A skin lesion imaged with a dermatoscope.
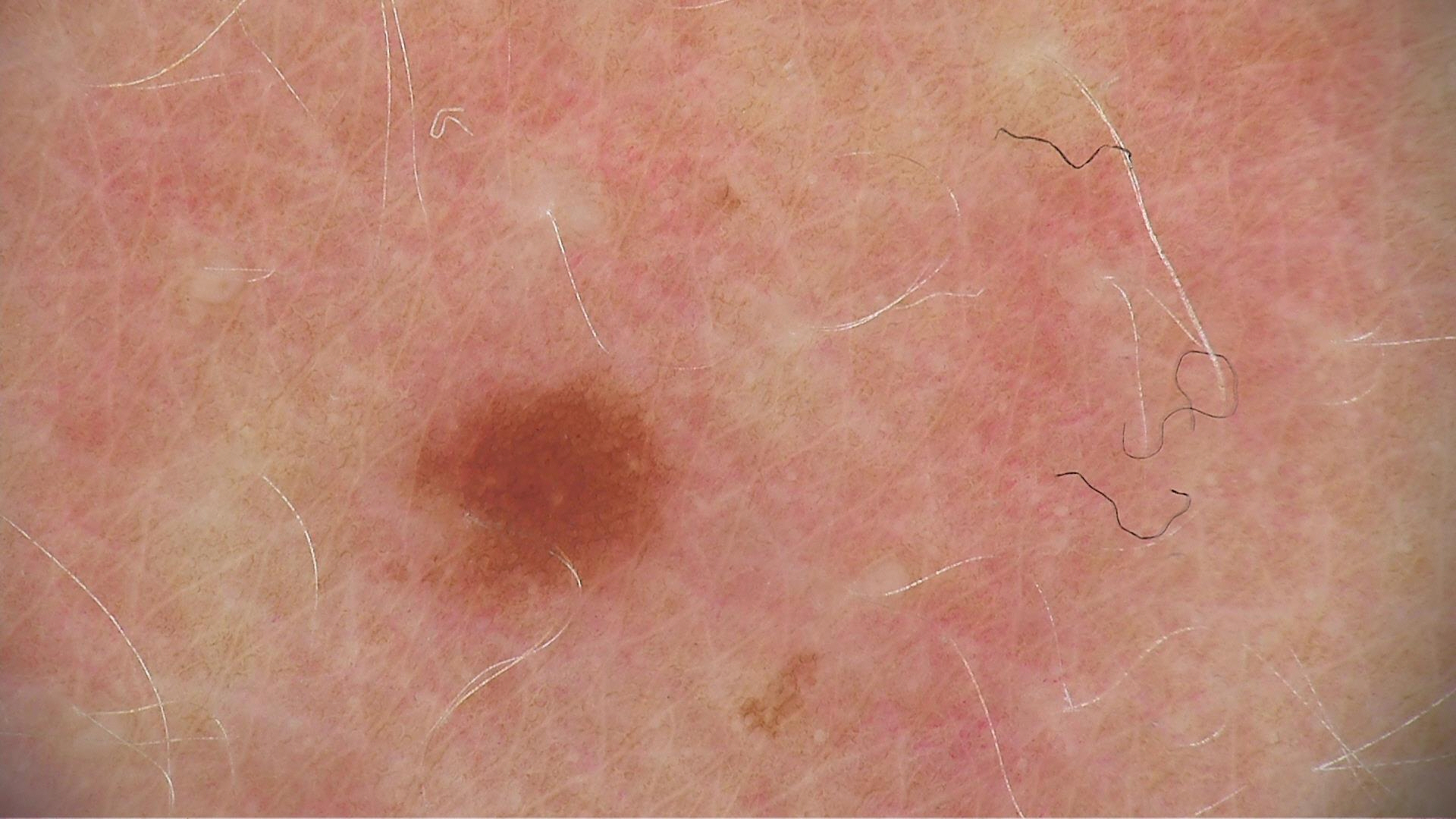{
  "diagnosis": {
    "name": "dysplastic junctional nevus",
    "code": "jd",
    "malignancy": "benign",
    "super_class": "melanocytic",
    "confirmation": "expert consensus"
  }
}